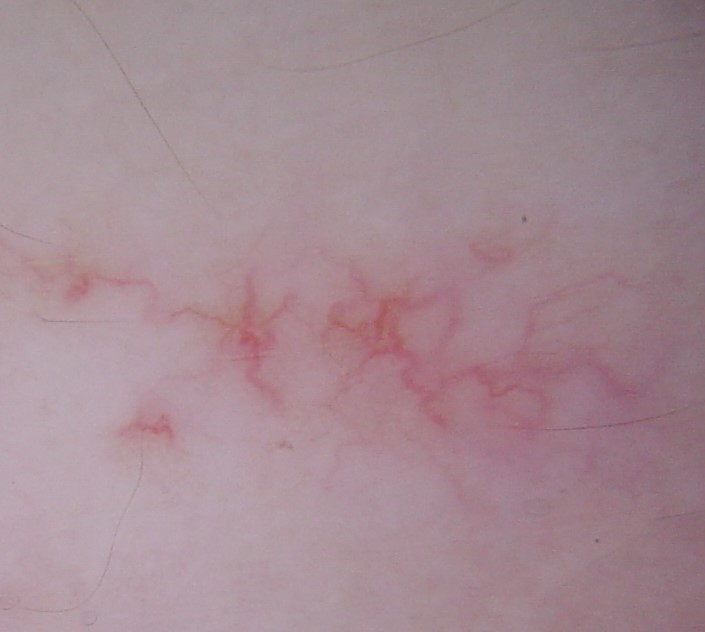Findings:
- class · spider angioma (expert consensus)